A dermoscopic photograph of a skin lesion.
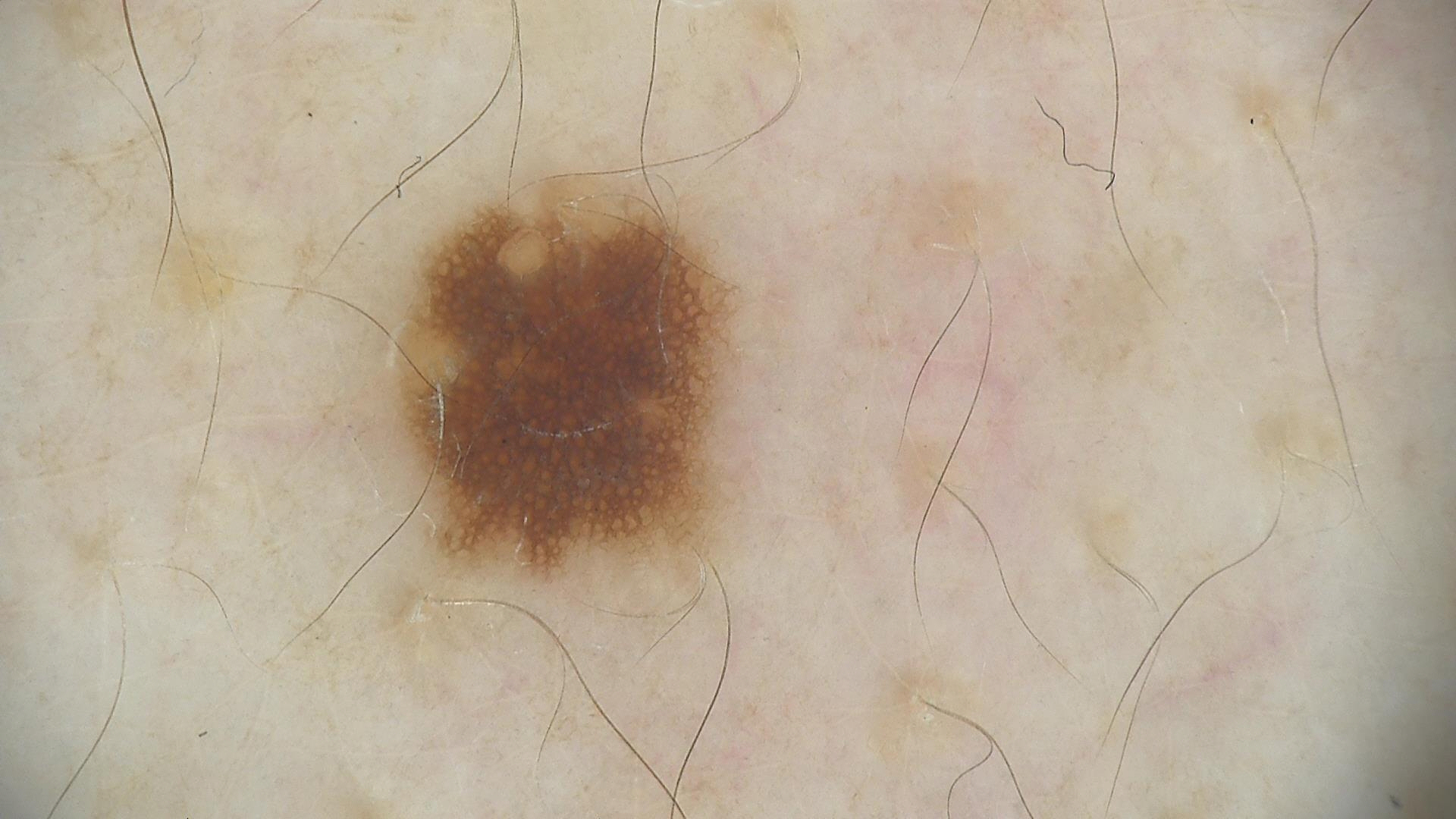diagnostic label=dysplastic junctional nevus (expert consensus).